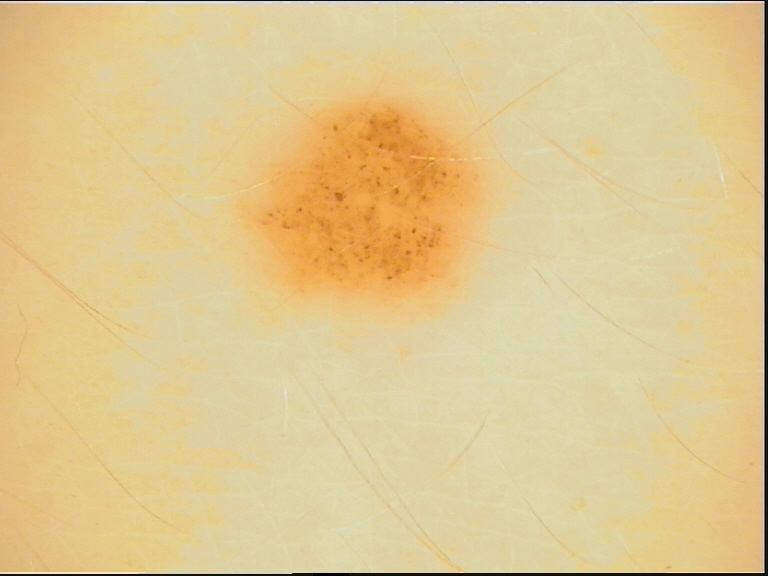Case:
– image type · dermatoscopy
– assessment · dysplastic junctional nevus (expert consensus)